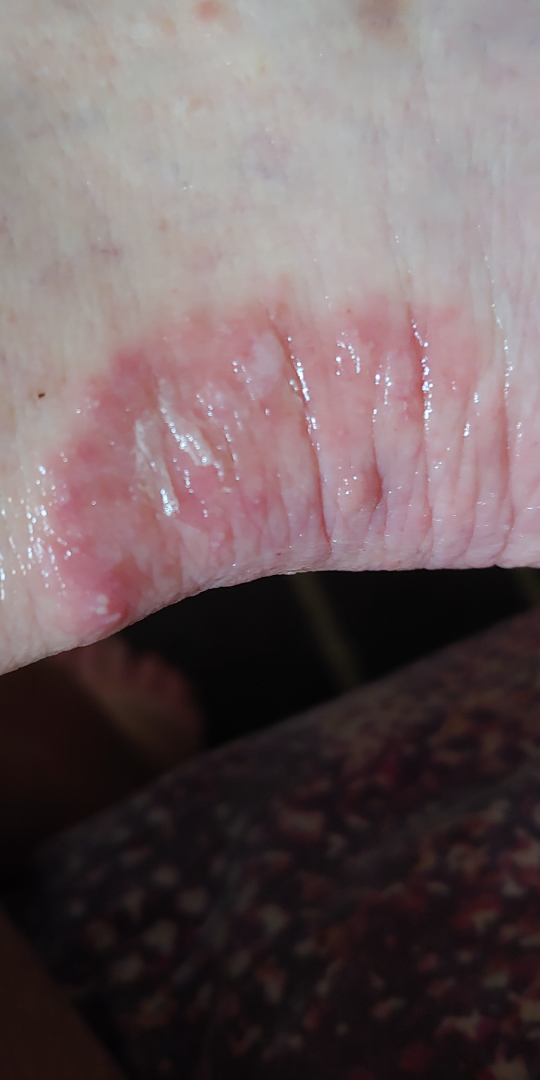Findings: The skin findings could not be characterized from the image.